A dermoscopic image of a skin lesion:
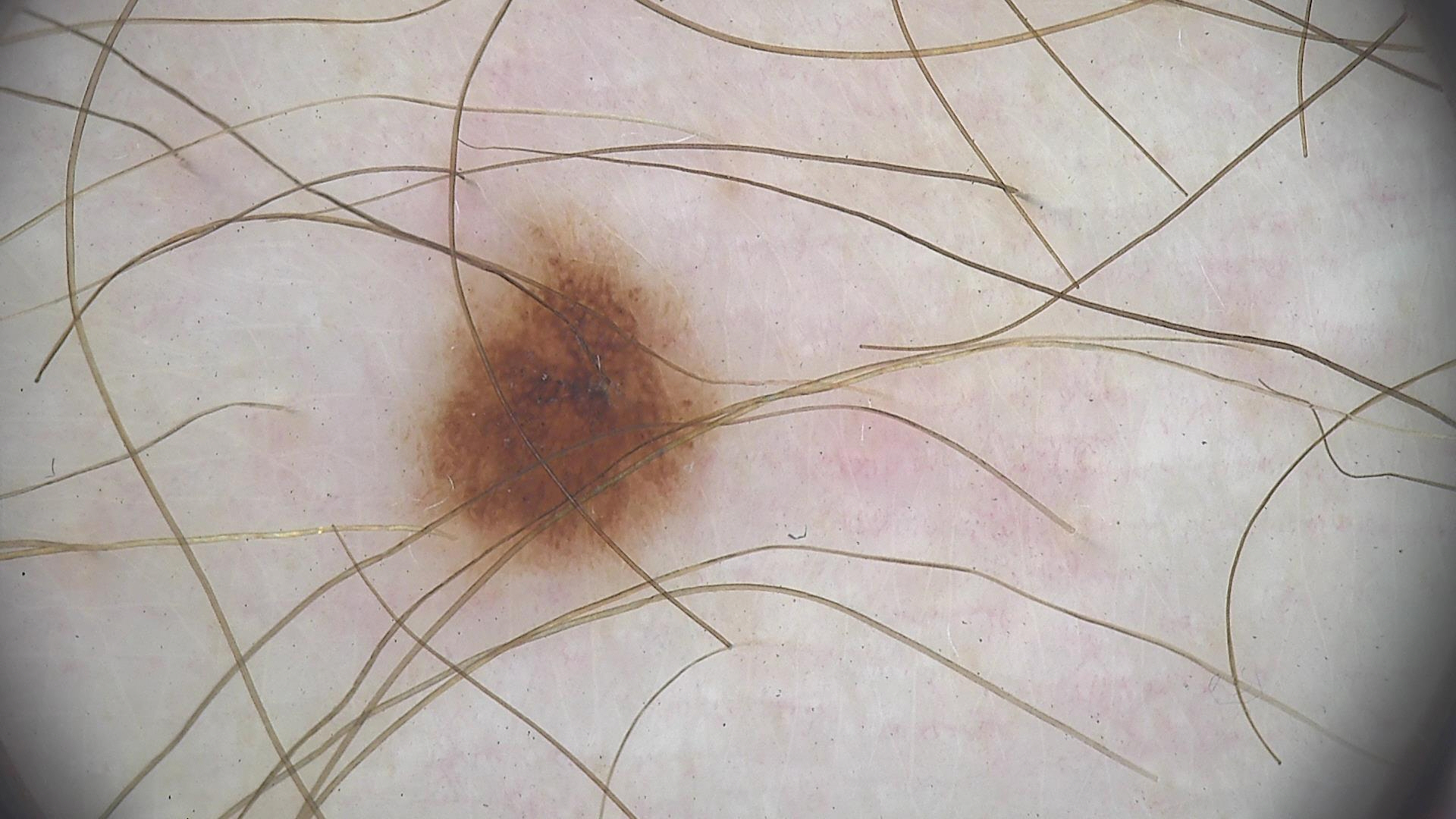Diagnosed as a benign lesion — a dysplastic junctional nevus.